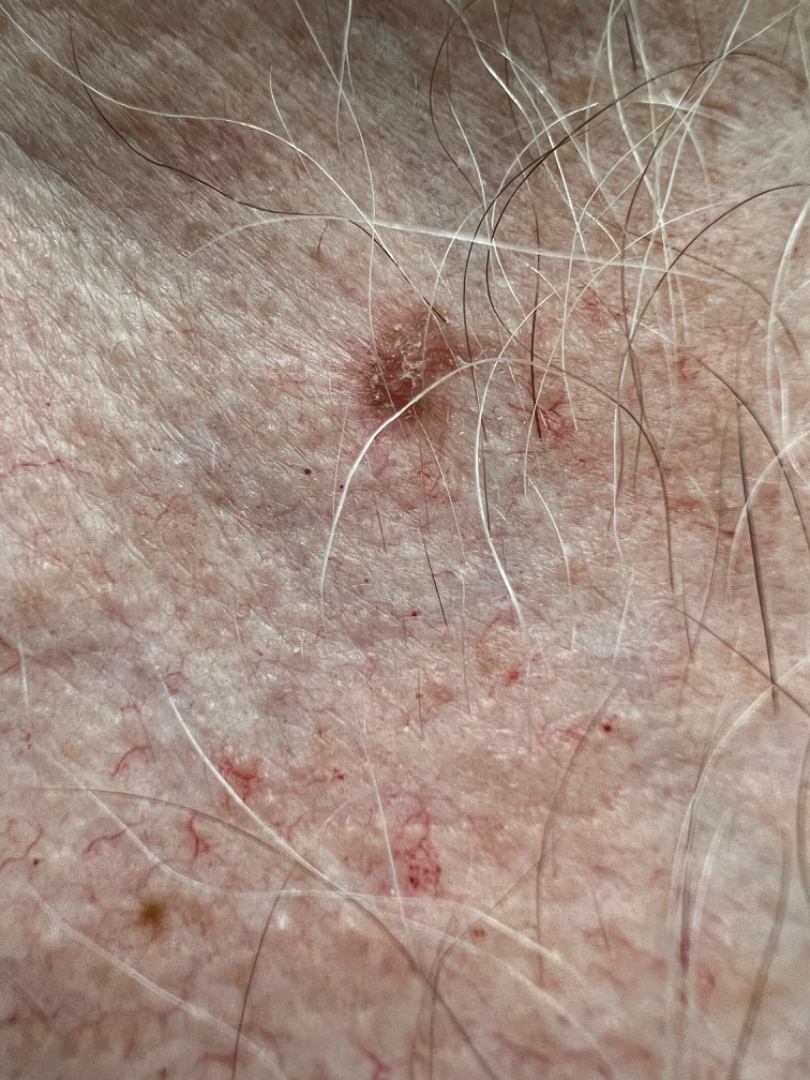History: The photograph is a close-up of the affected area. The lesion involves the head or neck. Skin tone: Fitzpatrick skin type I; lay graders estimated 2 on the Monk Skin Tone. Reported duration is more than one year. The patient is 50–59, male. The patient indicates the lesion is raised or bumpy and rough or flaky. Impression: On photographic review, Actinic Keratosis (weight 0.33); Basal Cell Carcinoma (weight 0.33); SCC/SCCIS (weight 0.33).